The photograph was taken at an angle — 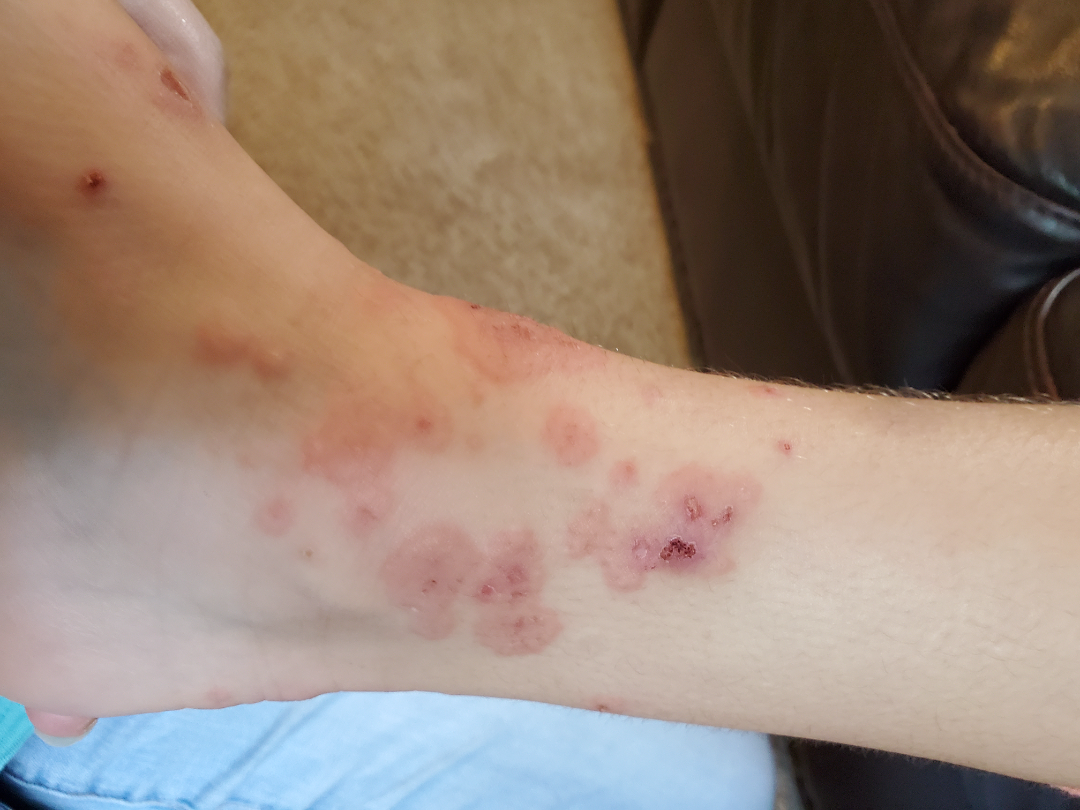Q: What is the differential diagnosis?
A: single-reviewer assessment: the impression is Erythema multiforme